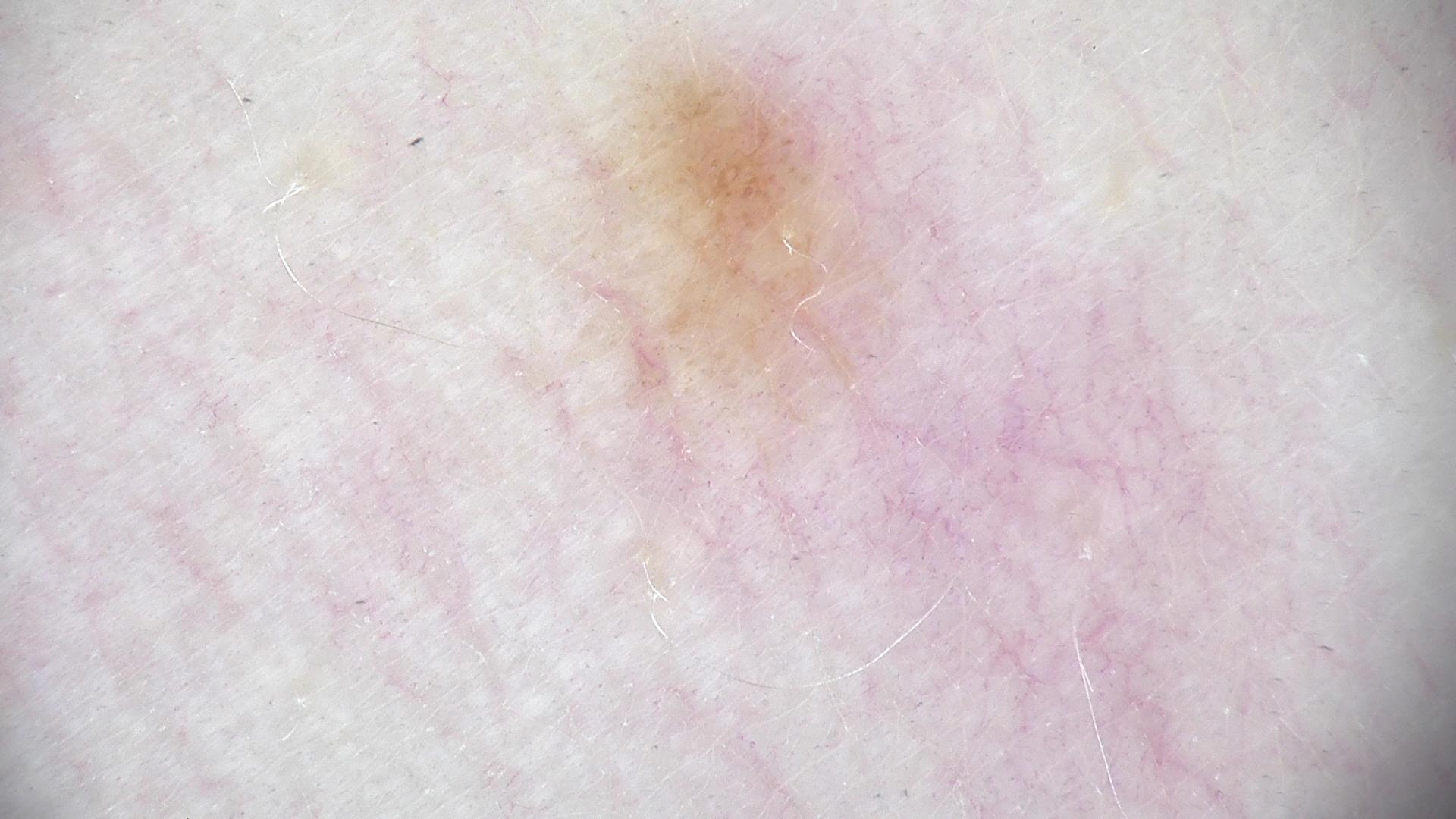Findings:
* label: junctional nevus (expert consensus)